A dermoscopy image of a single skin lesion.
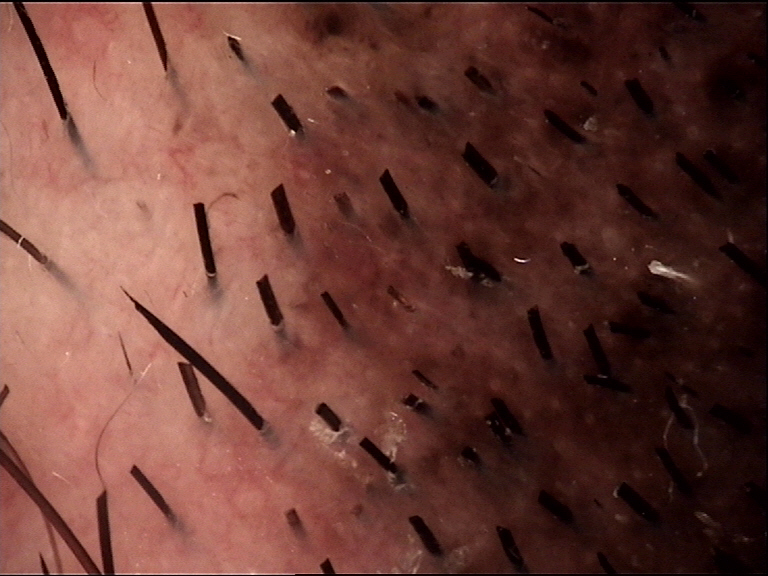- assessment · congenital compound nevus (expert consensus)